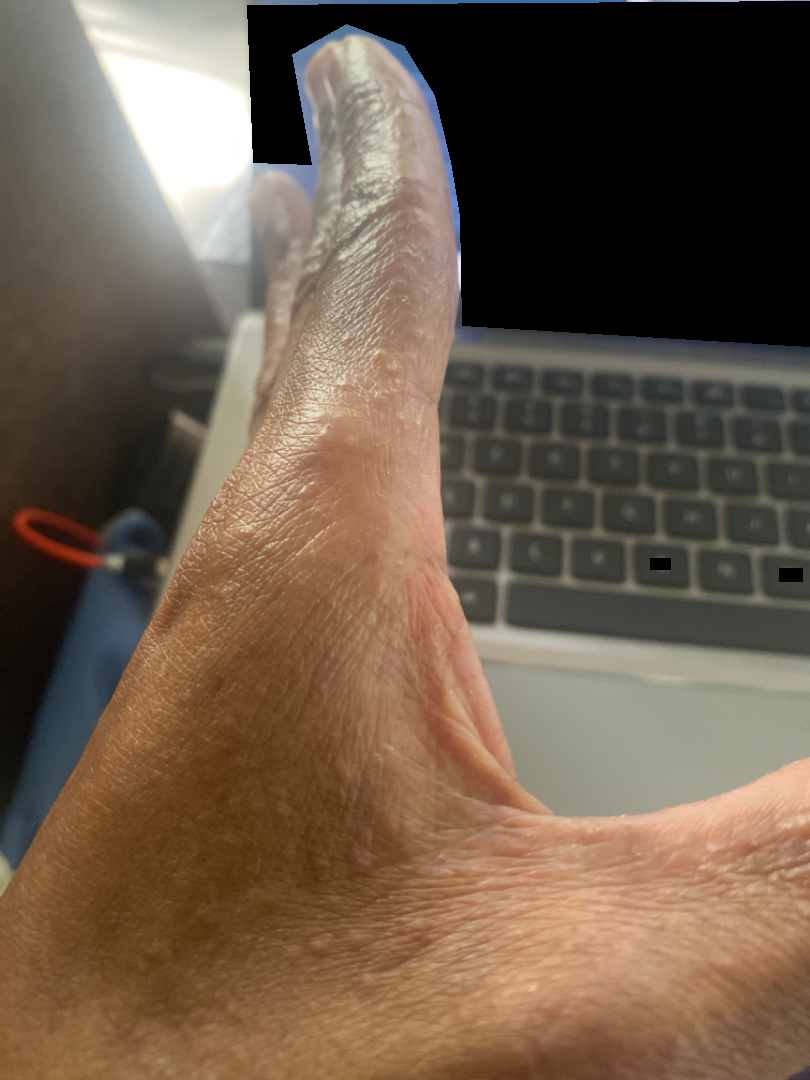The contributor is a male aged 30–39. Located on the back of the hand and palm. An image taken at an angle. On independent review by the dermatologists: Tinea (weight 0.33); Keratoderma (weight 0.33); Chronic dermatitis, NOS (weight 0.33).